A clinical close-up photograph of a skin lesion · history notes prior malignancy (patient or family), prior skin cancer (patient or family), and pesticide exposure · recorded as Fitzpatrick phototype II: 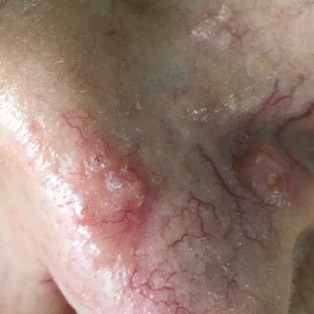The lesion is on the nose.
The patient reports that the lesion is elevated and itches.
On biopsy, the diagnosis was a malignancy — a basal cell carcinoma.